A skin lesion imaged with a dermatoscope — 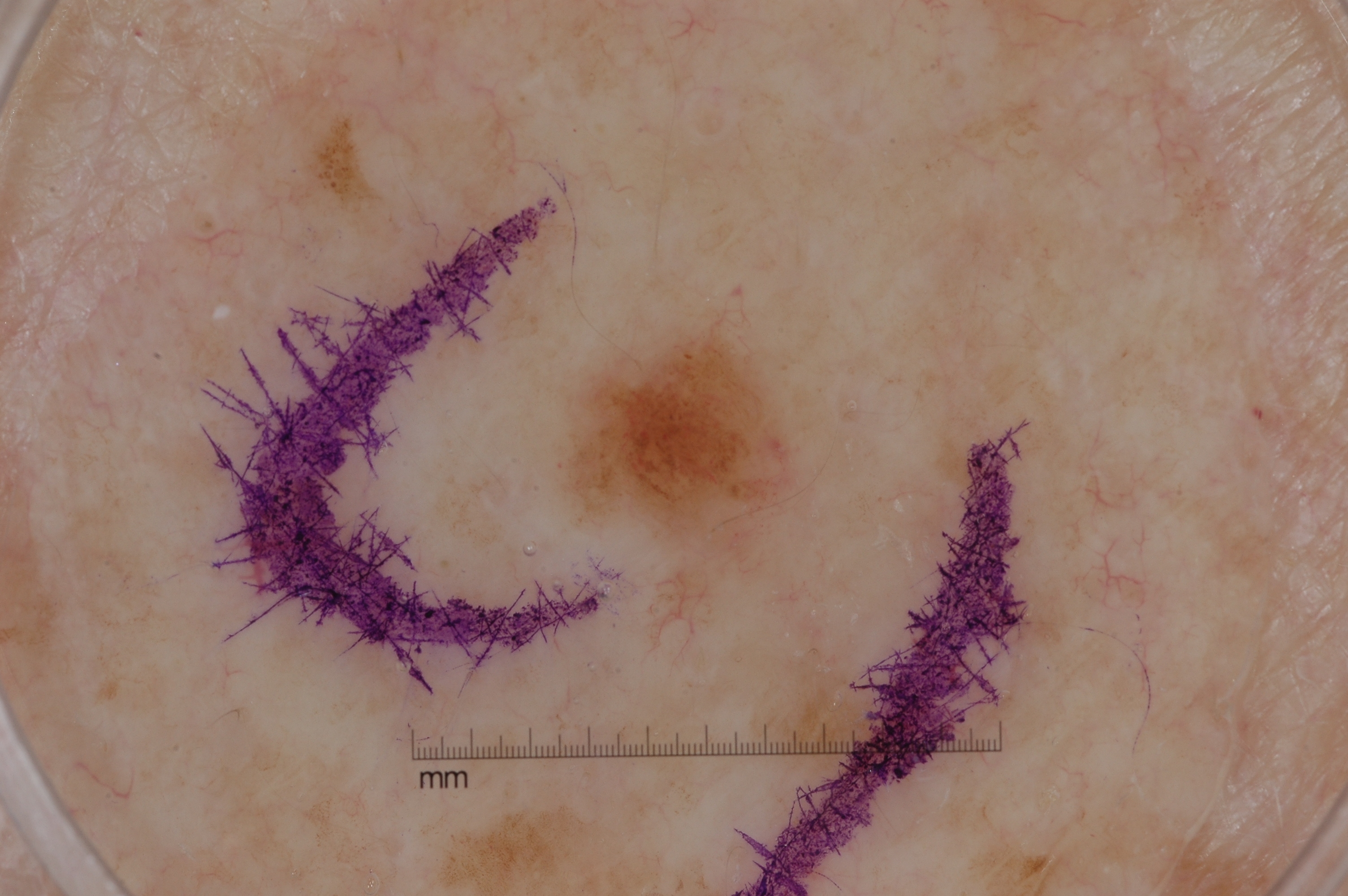Case summary: Dermoscopic assessment notes negative network and milia-like cysts; no streaks or pigment network. As (left, top, right, bottom), the lesion occupies the region bbox(562, 317, 794, 572). Impression: Diagnosed as a melanocytic nevus, a benign lesion.